The photograph is a close-up of the affected area:
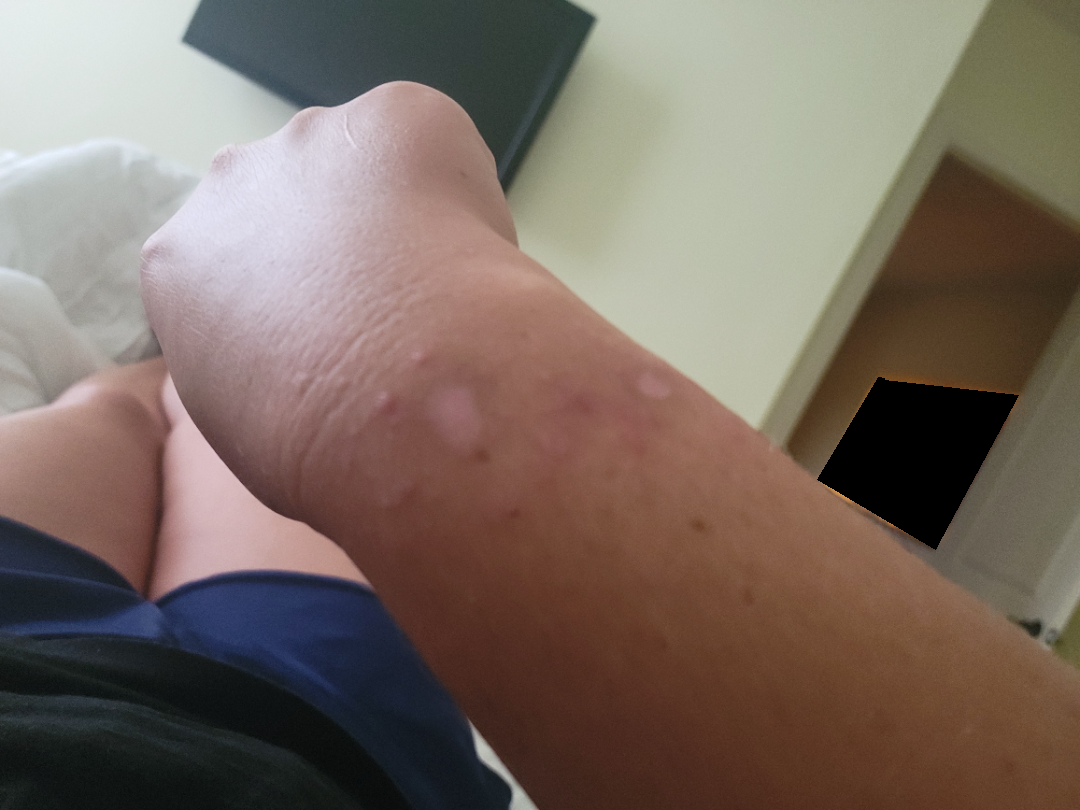| key | value |
|---|---|
| assessment | most likely Allergic Contact Dermatitis; also consider Acute and chronic dermatitis |